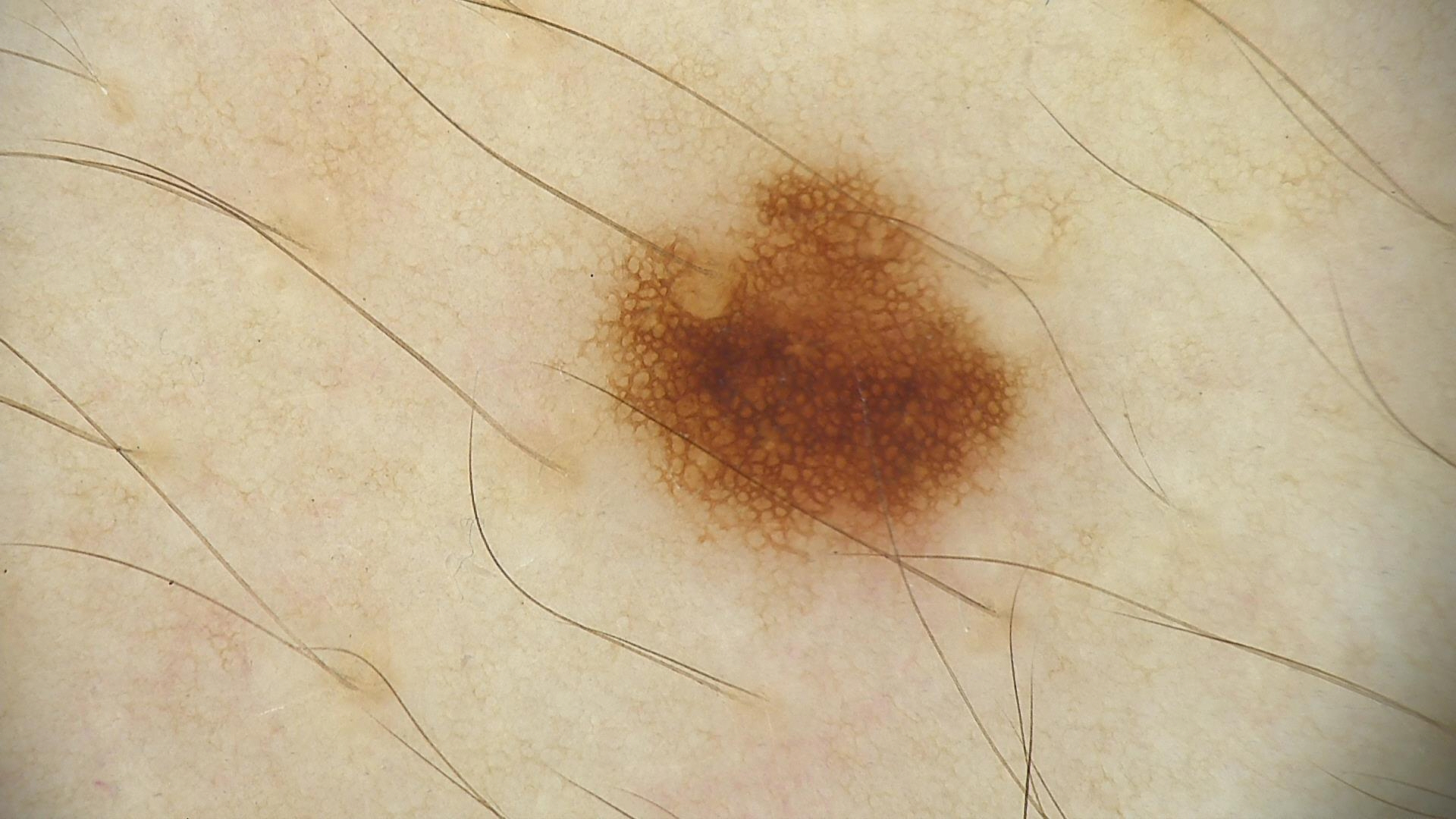A dermoscopic close-up of a skin lesion. Classified as a dysplastic junctional nevus.